Recorded as Fitzpatrick II; a wide-field clinical photograph of a skin lesion; the chart documents a previous melanoma but no first-degree relative with melanoma; a male patient roughly 75 years of age.
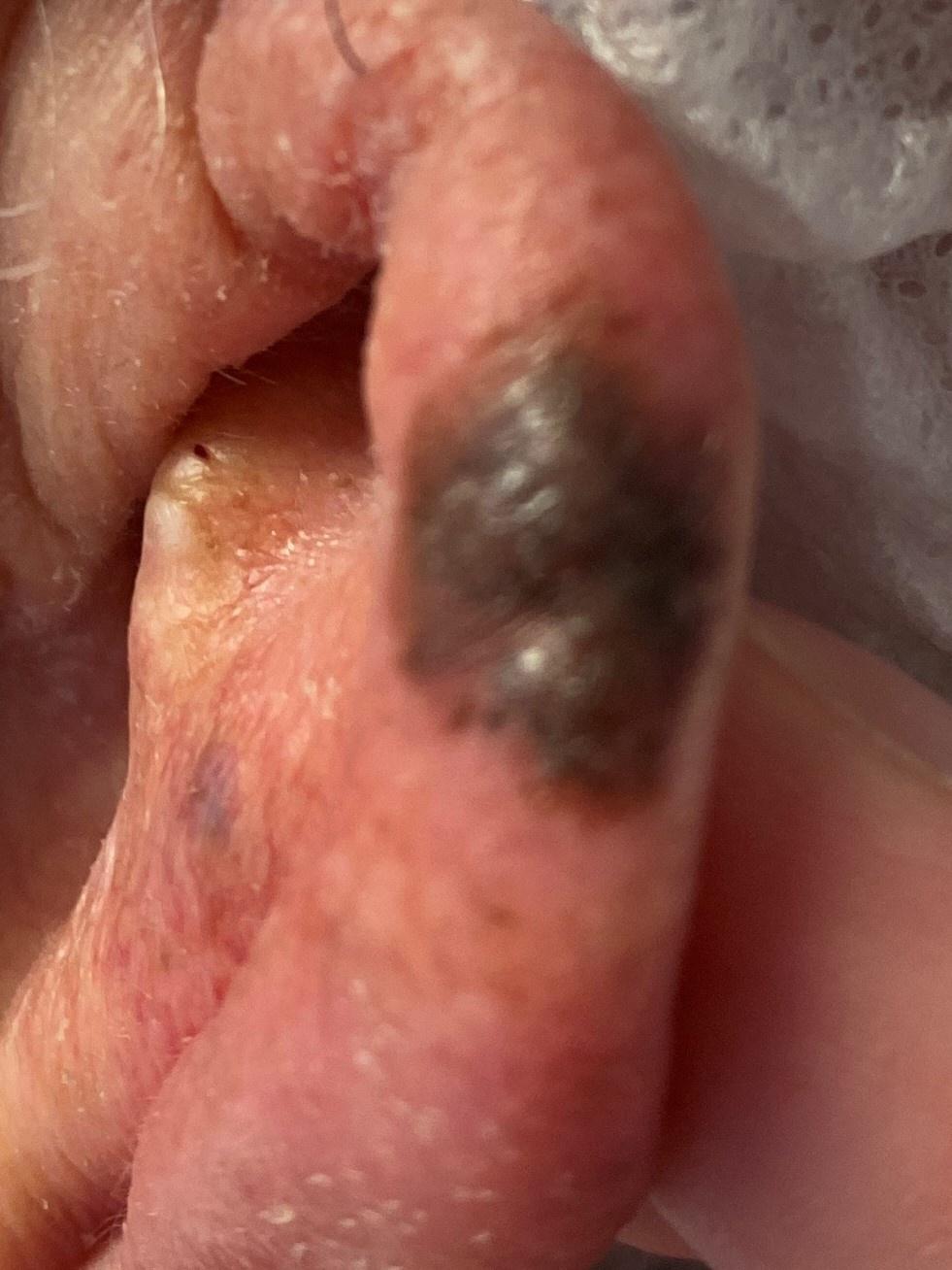- body site — the head or neck
- pathology — Melanoma (biopsy-proven)